A patient in their mid-30s · a clinical photo of a skin lesion taken with a smartphone: 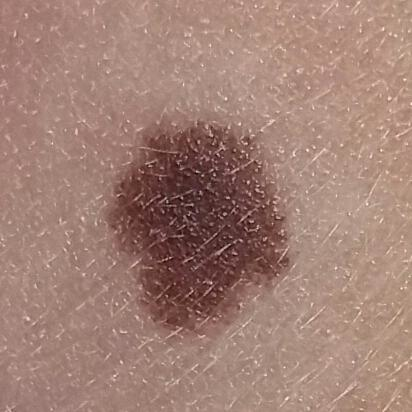Q: Where on the body is the lesion?
A: an ear
Q: What does the patient describe?
A: none reported
Q: What is this lesion?
A: nevus (clinical consensus)